The condition has been present for less than one week; no constitutional symptoms were reported; the contributor notes bothersome appearance, bleeding, pain and itching; the photo was captured at an angle; the leg is involved; male contributor, age 30–39 — 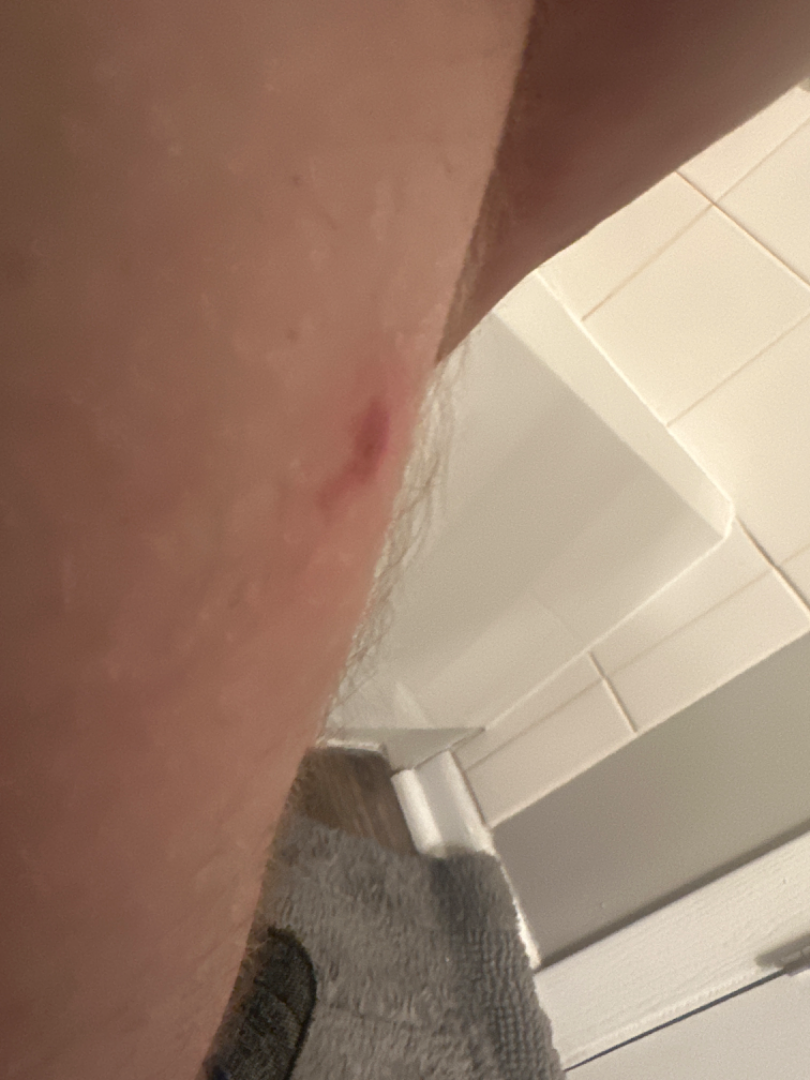Impression: The differential is split between Inflicted skin lesions, Insect Bite and Localized skin infection.